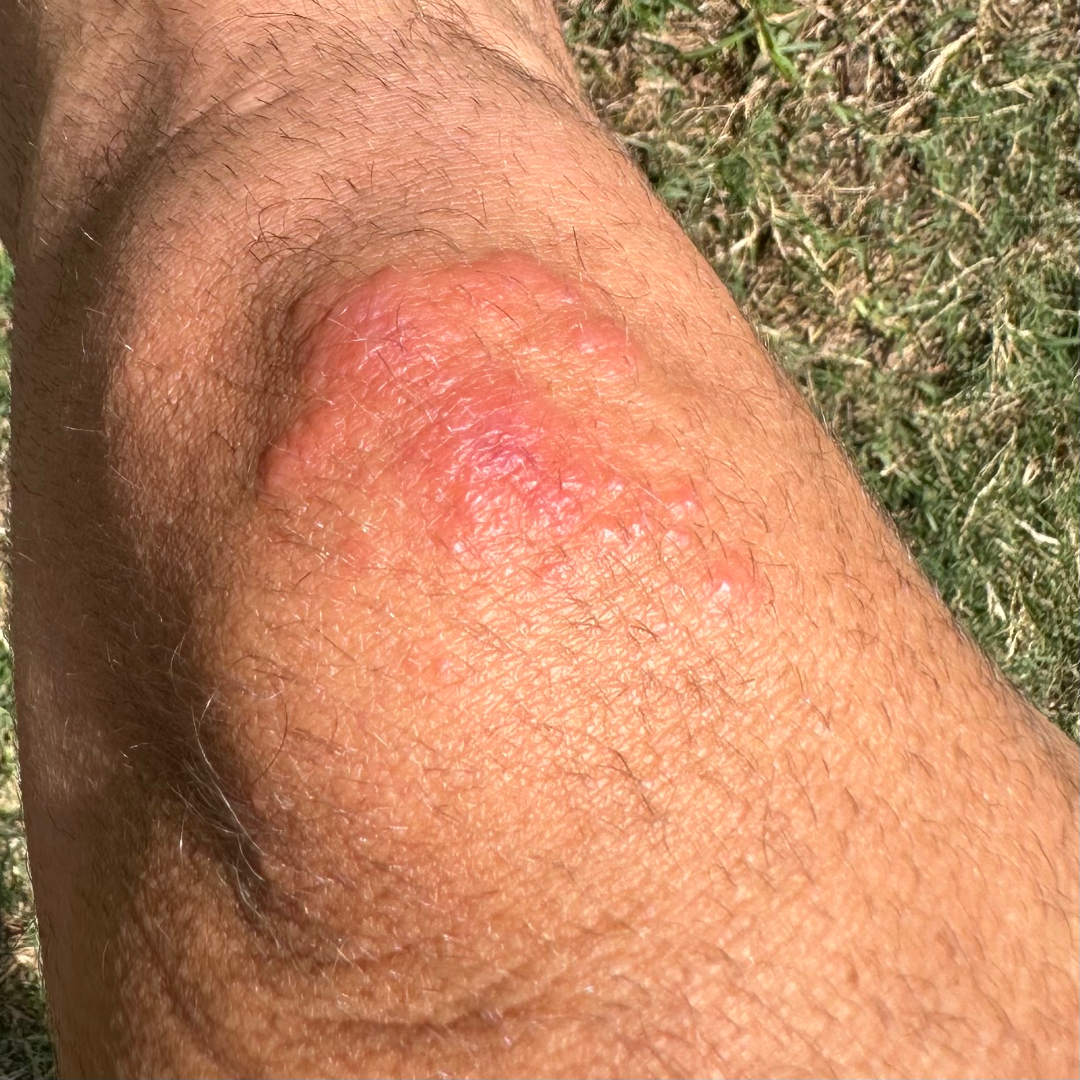The image was not sufficient for the reviewer to characterize the skin condition.
Texture is reported as raised or bumpy.
The photograph was taken at a distance.
Self-categorized by the patient as a rash.
No relevant systemic symptoms.
The contributor reports enlargement, bothersome appearance and itching.
Located on the arm and leg.
The contributor reports the condition has been present for less than one week.
The patient is a male aged 40–49.
Non-clinician graders estimated MST 3–4.